The patient was assessed as Fitzpatrick skin type II · a clinical photograph showing a skin lesion · a female subject aged 84 · the chart notes prior malignancy (patient or family) — 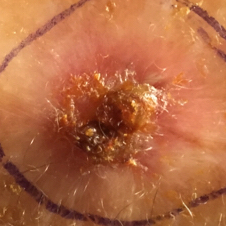  lesion_location: a forearm
  symptoms:
    present:
      - elevation
      - pain
      - itching
      - bleeding
  diagnosis:
    name: squamous cell carcinoma
    code: SCC
    malignancy: malignant
    confirmation: histopathology